A dermatoscopic image of a skin lesion: 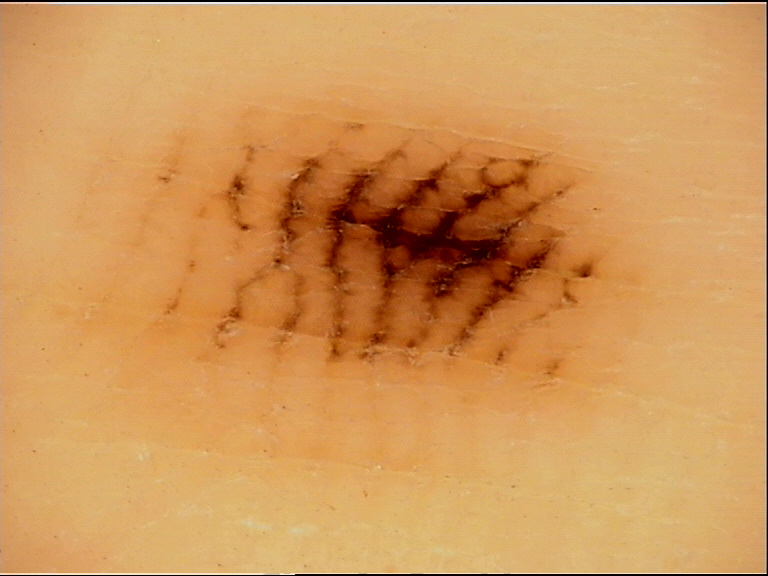Case:
The morphology is that of a banal lesion.
Impression:
The diagnostic label was an acral junctional nevus.